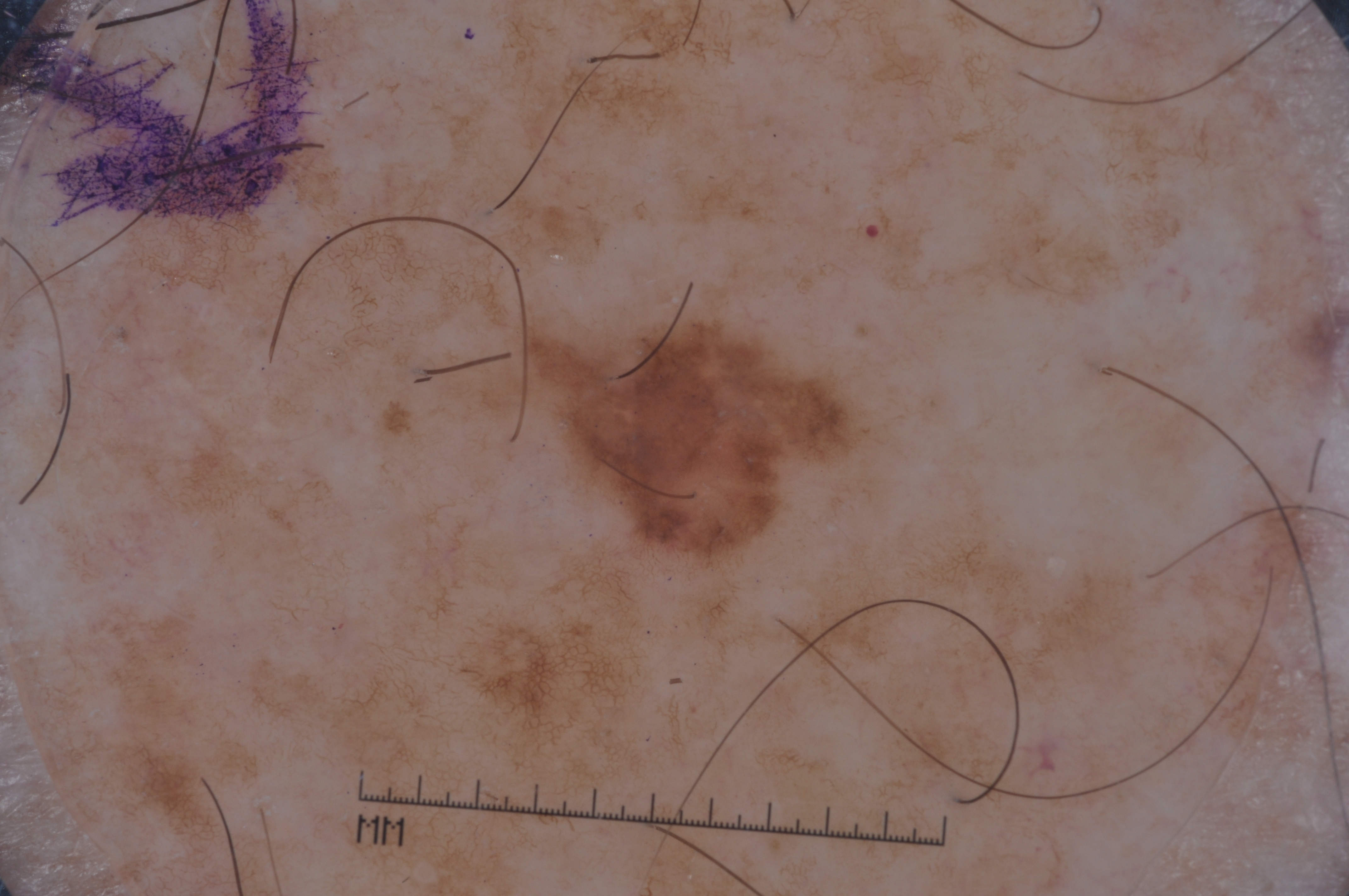<case>
<image>
  <modality>dermoscopy</modality>
</image>
<lesion_location>
  <bbox_xyxy>517, 315, 864, 553</bbox_xyxy>
</lesion_location>
<dermoscopic_features>
  <present>pigment network, negative network</present>
  <absent>streaks, milia-like cysts</absent>
</dermoscopic_features>
<diagnosis>
  <name>melanoma</name>
  <malignancy>malignant</malignancy>
  <lineage>melanocytic</lineage>
  <provenance>histopathology</provenance>
</diagnosis>
</case>